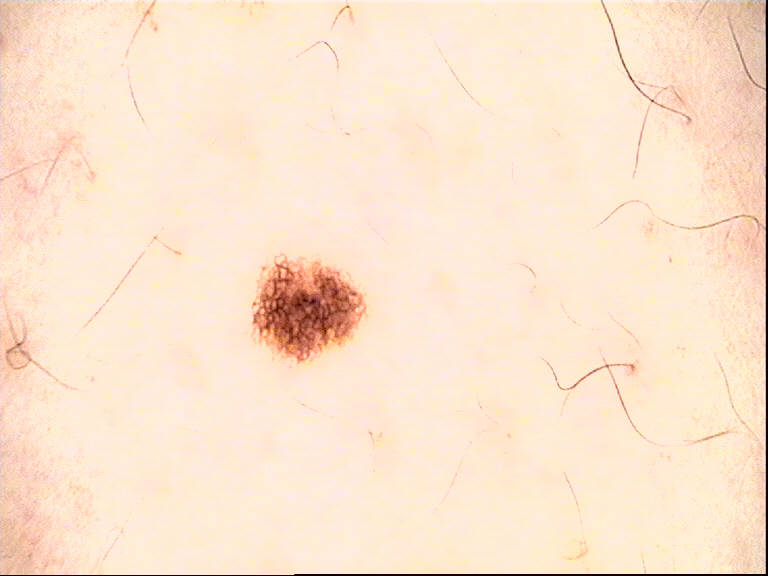imaging: dermoscopy | assessment: dysplastic junctional nevus (expert consensus).